A skin lesion imaged with a dermatoscope: 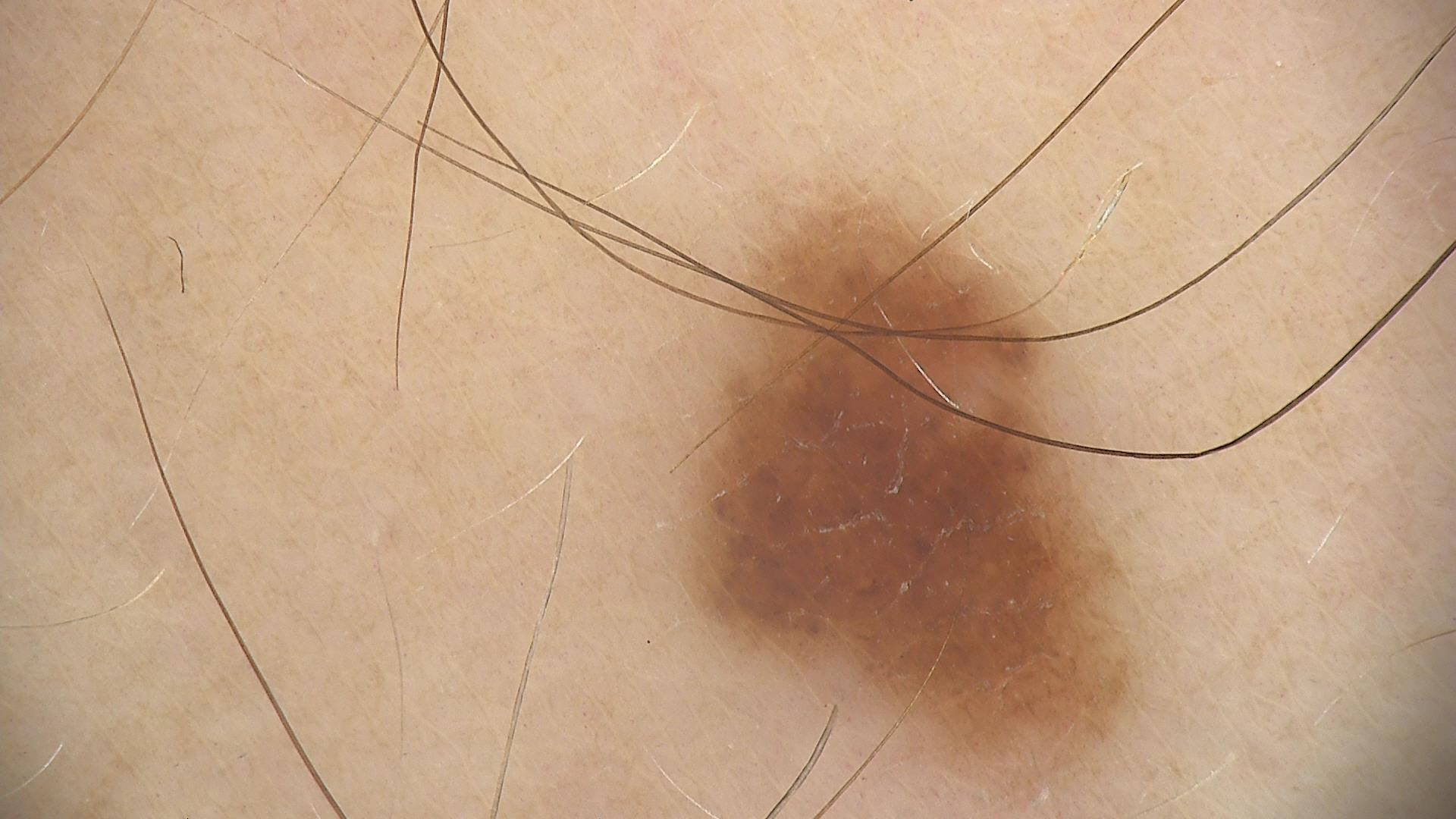<dermoscopy>
<diagnosis>
<name>dysplastic junctional nevus</name>
<code>jd</code>
<malignancy>benign</malignancy>
<super_class>melanocytic</super_class>
<confirmation>expert consensus</confirmation>
</diagnosis>
</dermoscopy>